A dermoscopic image of a skin lesion.
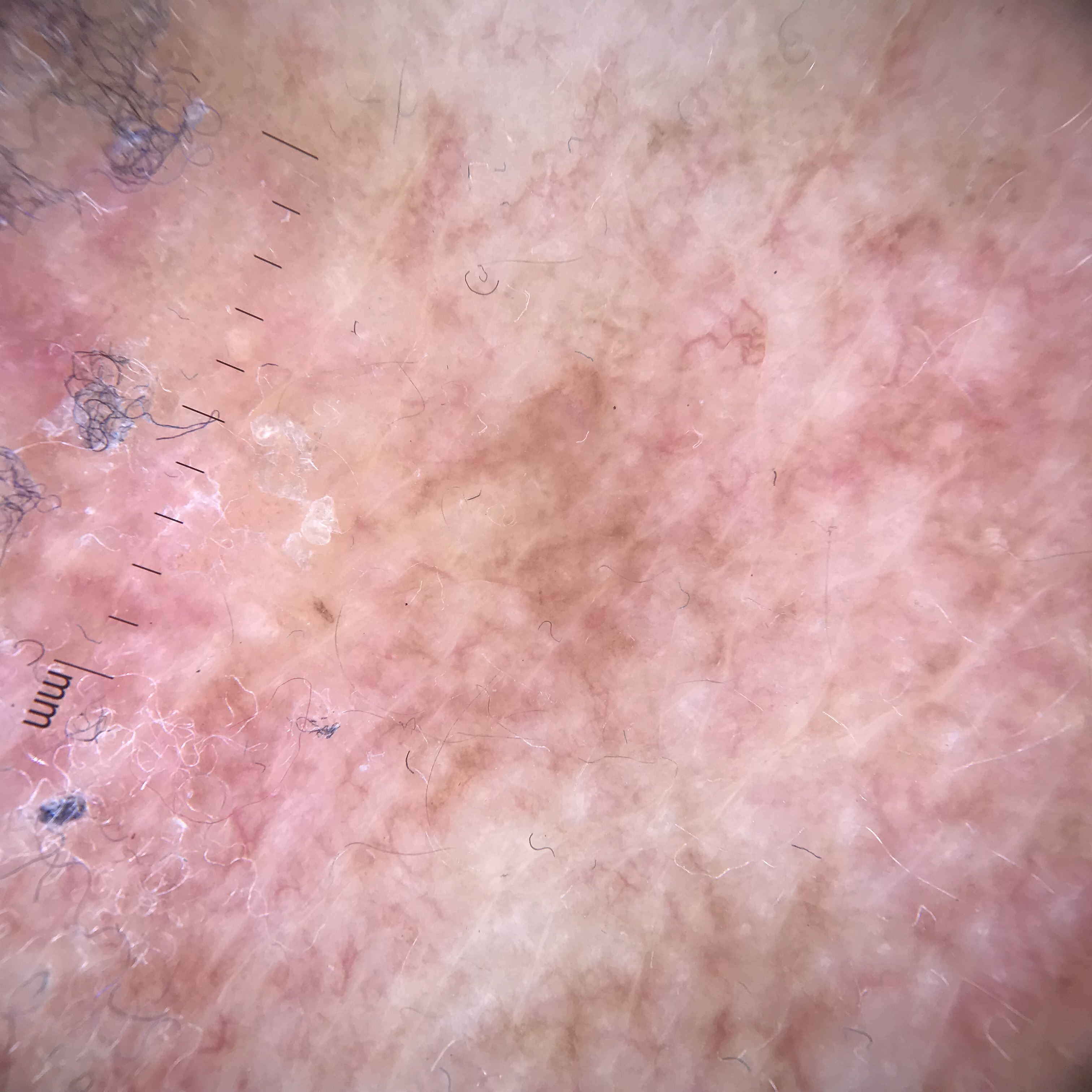Classified as a premalignant lesion — an actinic keratosis.